This is a close-up image: 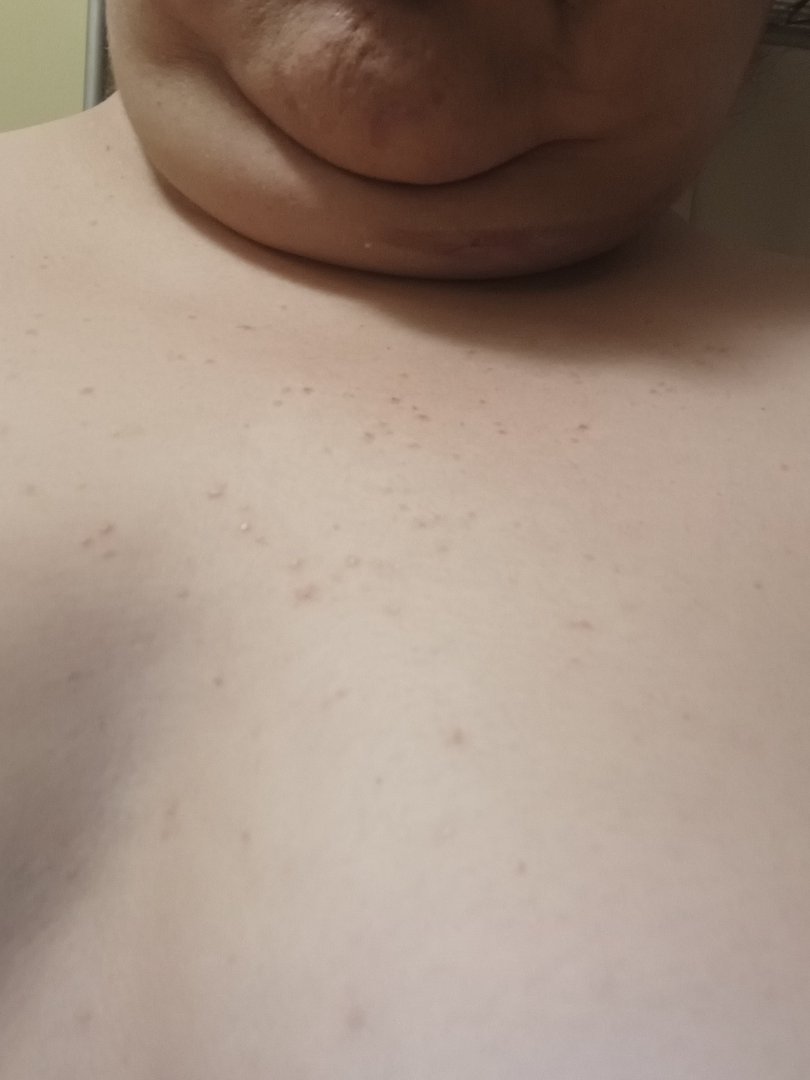assessment — indeterminate.